A dermoscopic photograph of a skin lesion.
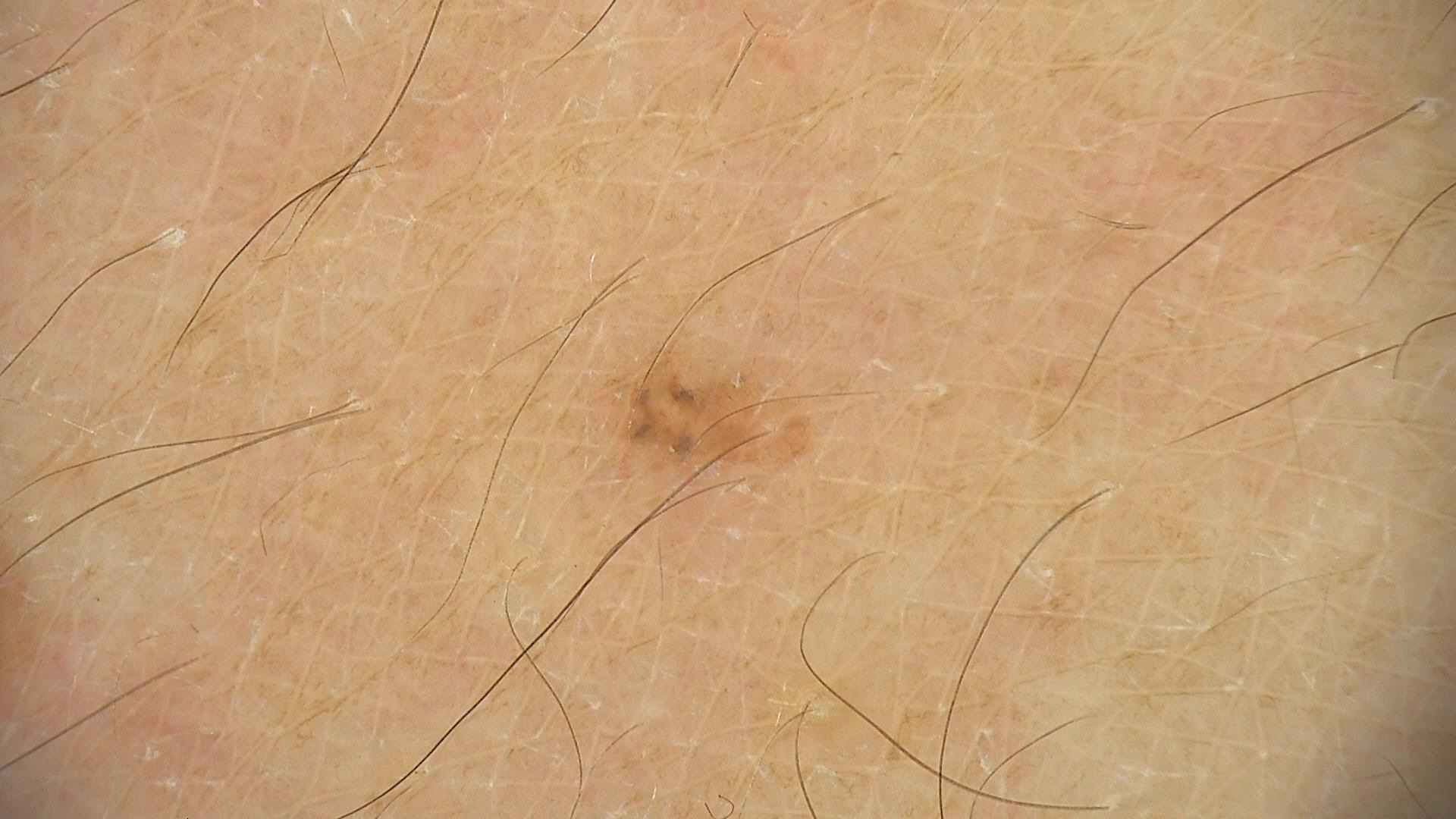Classified as a dysplastic junctional nevus.